A contact-polarized dermoscopy image of a skin lesion · a male subject about 70 years old · the patient is Fitzpatrick skin type II: 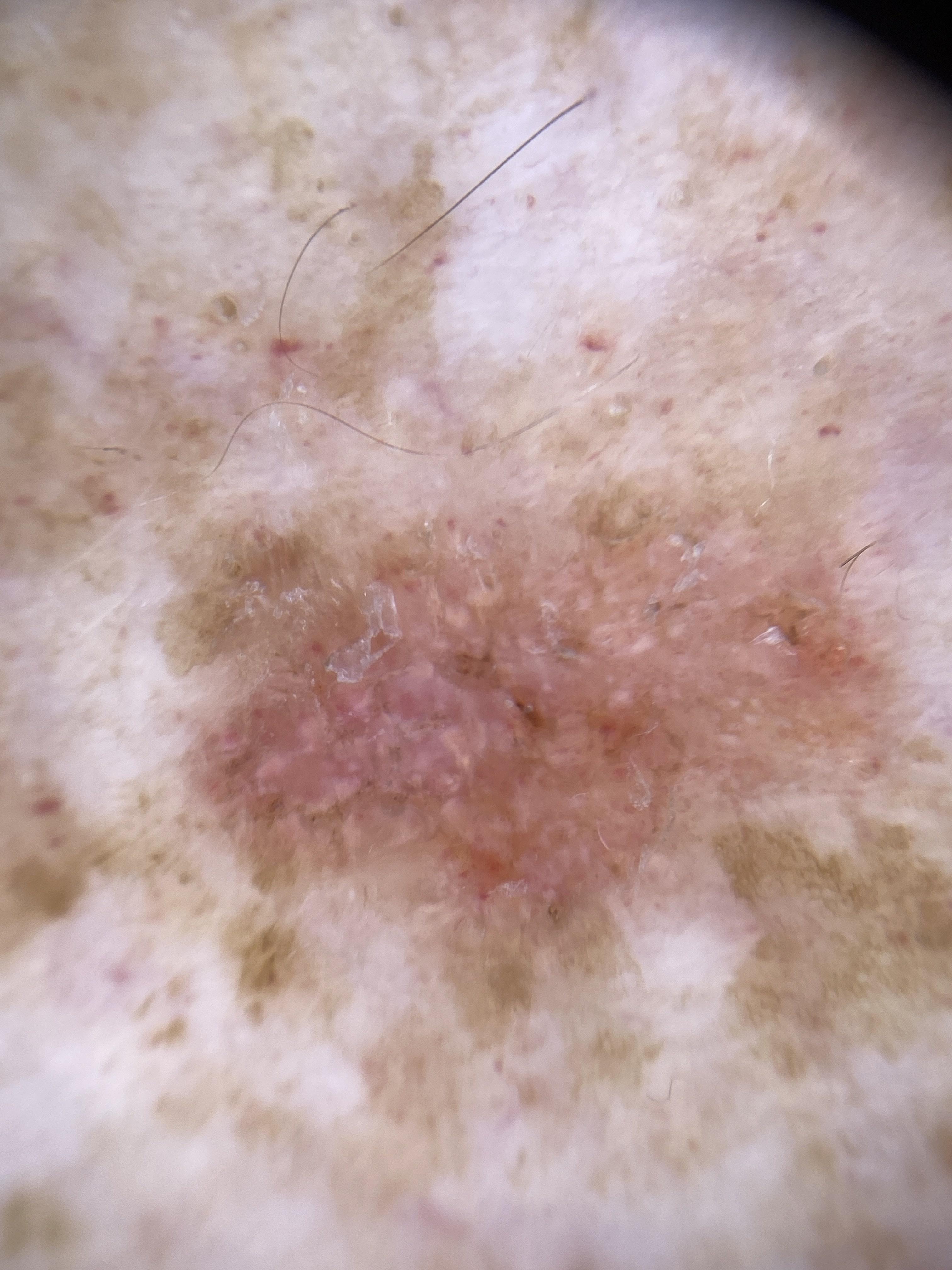<case>
  <lesion_location>
    <region>a lower extremity</region>
  </lesion_location>
  <diagnosis>
    <name>Basal cell carcinoma</name>
    <malignancy>malignant</malignancy>
    <confirmation>histopathology</confirmation>
    <lineage>adnexal</lineage>
  </diagnosis>
</case>